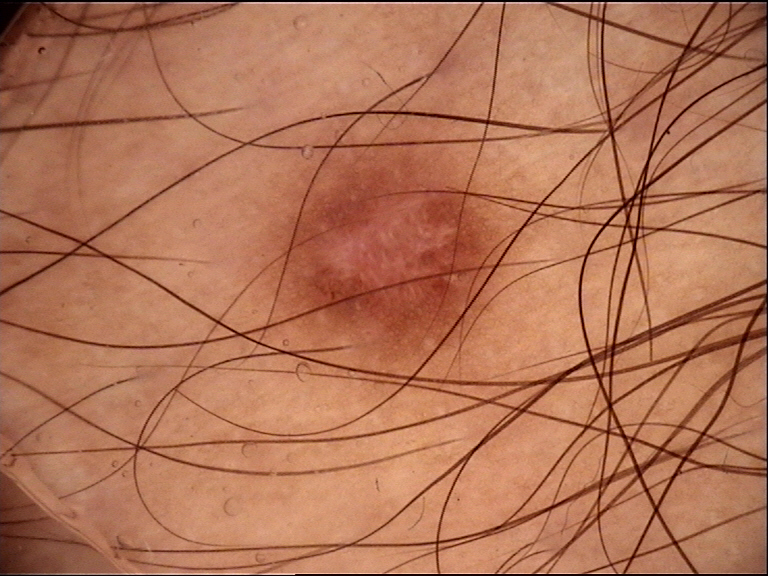Q: What was the diagnostic impression?
A: dermatofibroma (expert consensus)